The photograph was taken at an angle · the patient described the issue as a rash · the lesion involves the leg · texture is reported as rough or flaky · the contributor is a female aged 40–49 · the patient did not report lesion symptoms · Fitzpatrick IV: 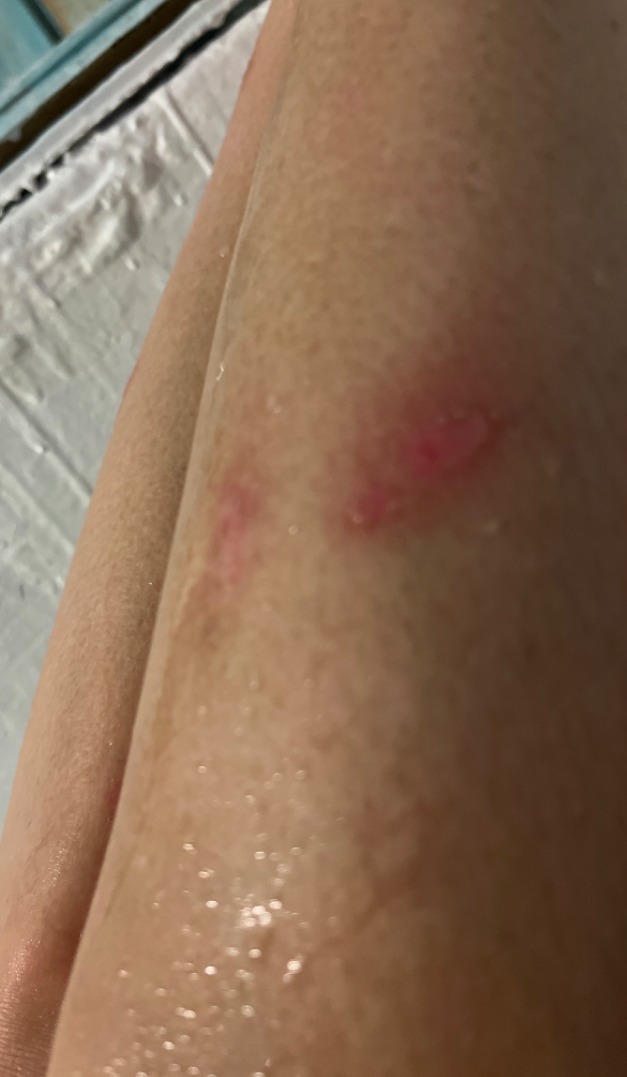diagnostic considerations=the leading impression is Abrasion, scrape, or scab; possibly Burn erythema of lower leg